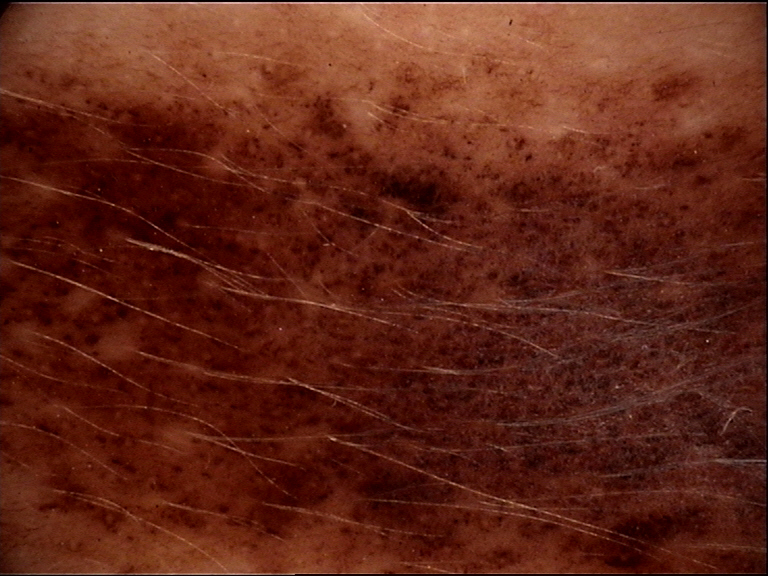category = banal
diagnostic label = congenital compound nevus (expert consensus)